A male patient age 62. The patient describes having few moles overall. A clinical close-up of a skin lesion.
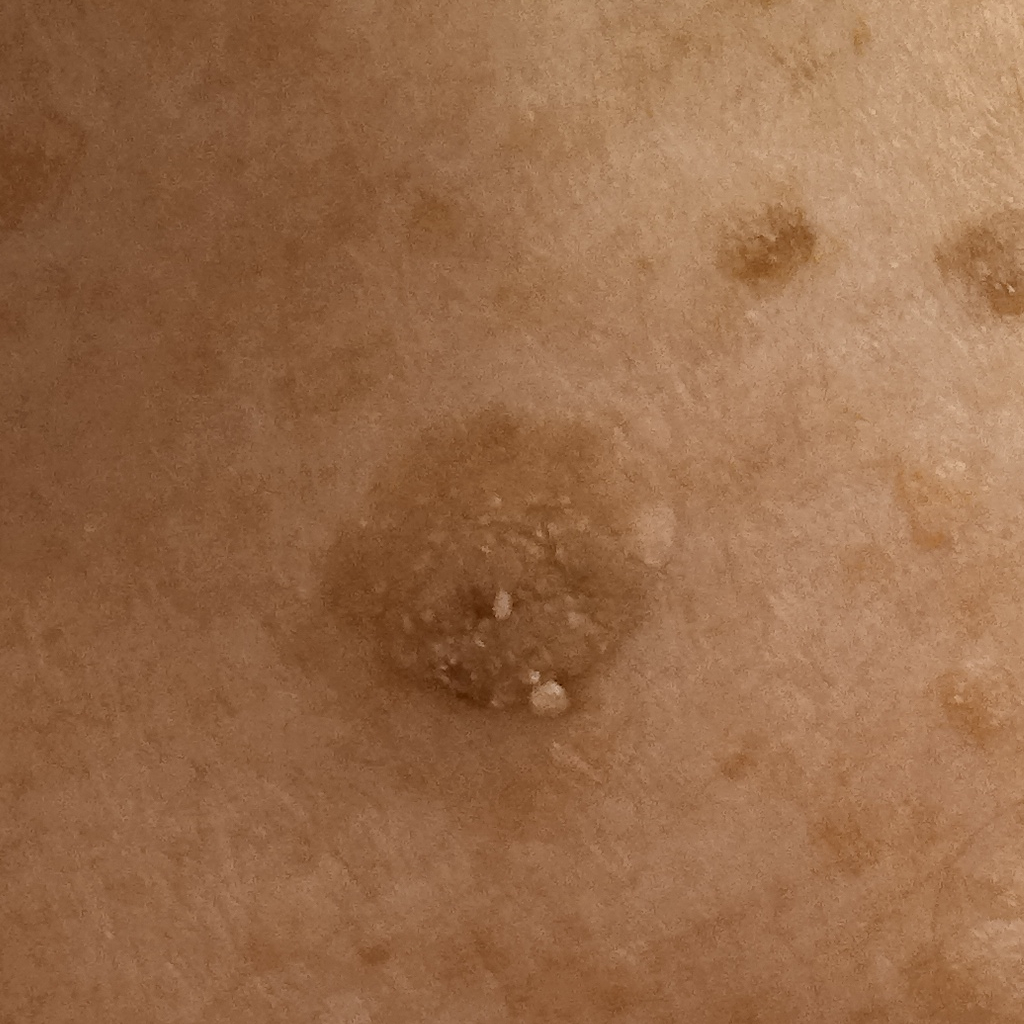Findings:
• location · the torso
• diameter · 11.3 mm
• diagnostic label · seborrheic keratosis (dermatologist consensus)